The photo was captured at an angle, the affected area is the arm: 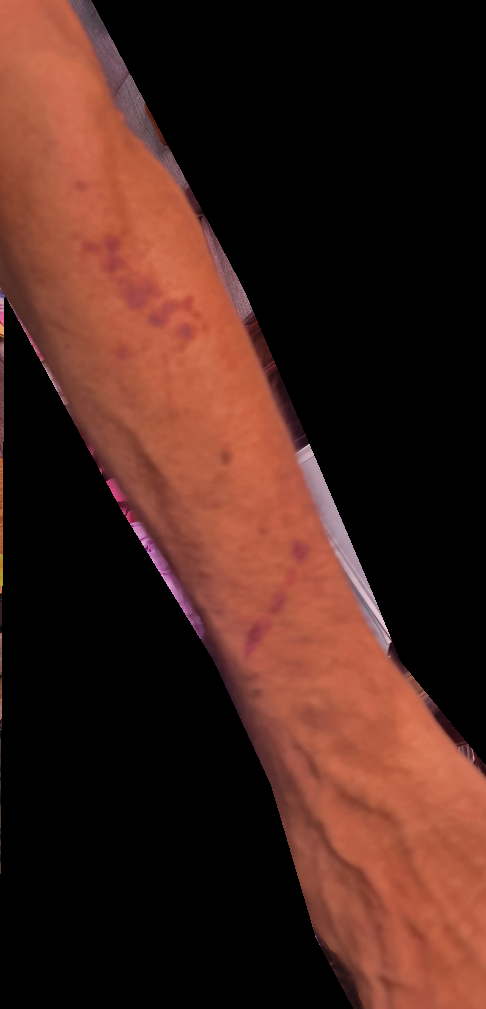The patient reports the lesion is flat. Reported duration is about one day. On dermatologist assessment of the image, in keeping with ecchymoses.